A patient in their early 60s:
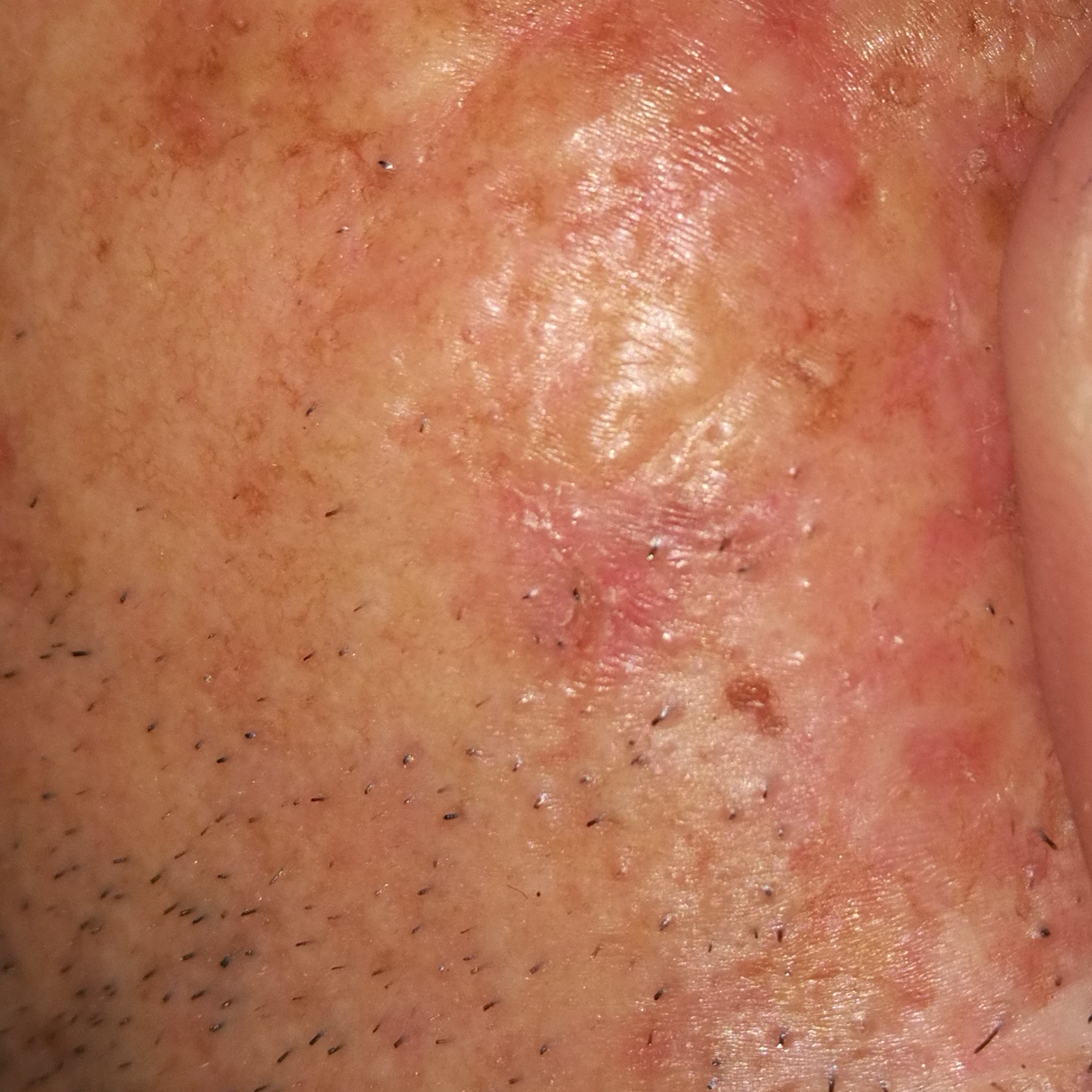<record>
  <lesion_location>the face</lesion_location>
  <diagnosis>
    <name>actinic keratosis</name>
    <code>ACK</code>
    <malignancy>indeterminate</malignancy>
    <confirmation>clinical consensus</confirmation>
  </diagnosis>
</record>